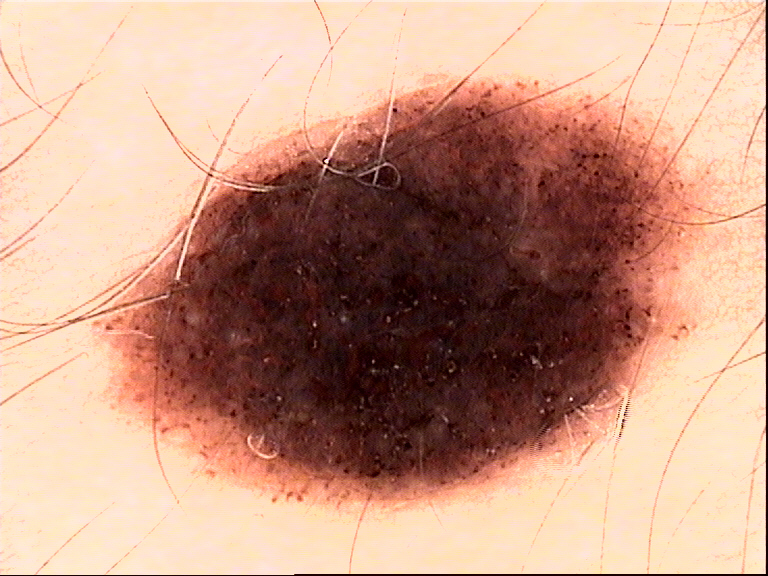diagnosis — dysplastic compound nevus (expert consensus).